The photograph is a close-up of the affected area:
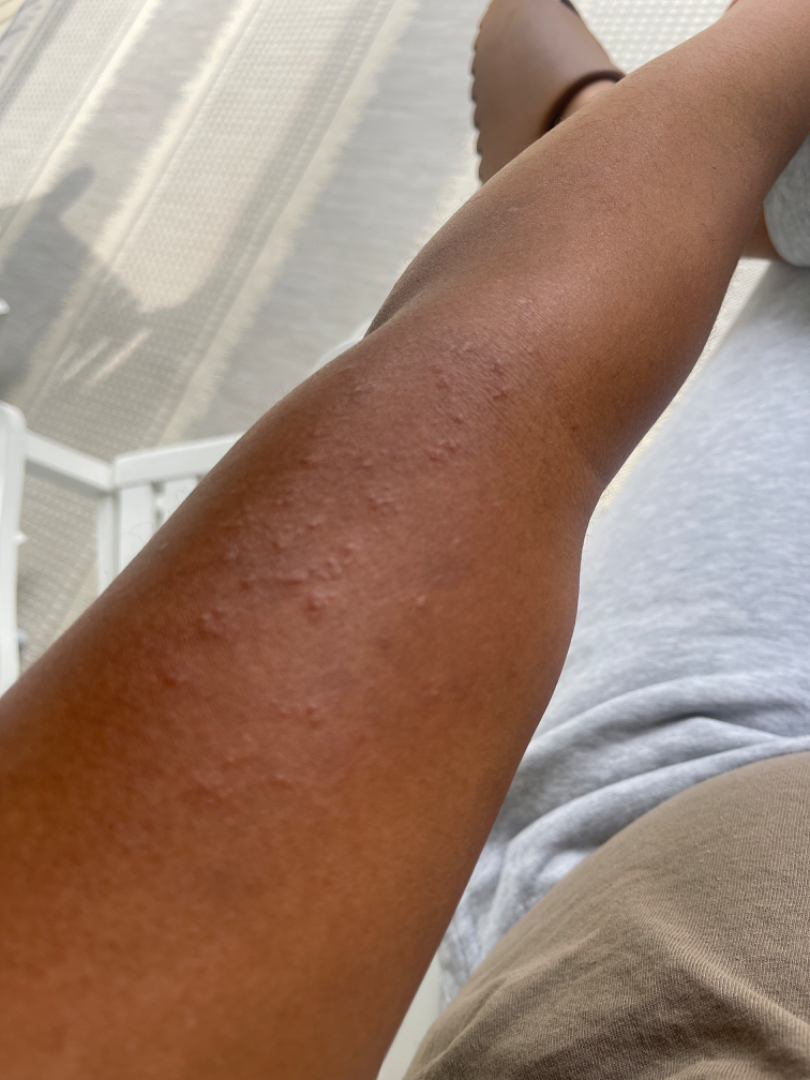Notes:
– assessment · could not be assessed